The subject is a female in their mid- to late 80s or older, this is a dermoscopic photograph of a skin lesion:
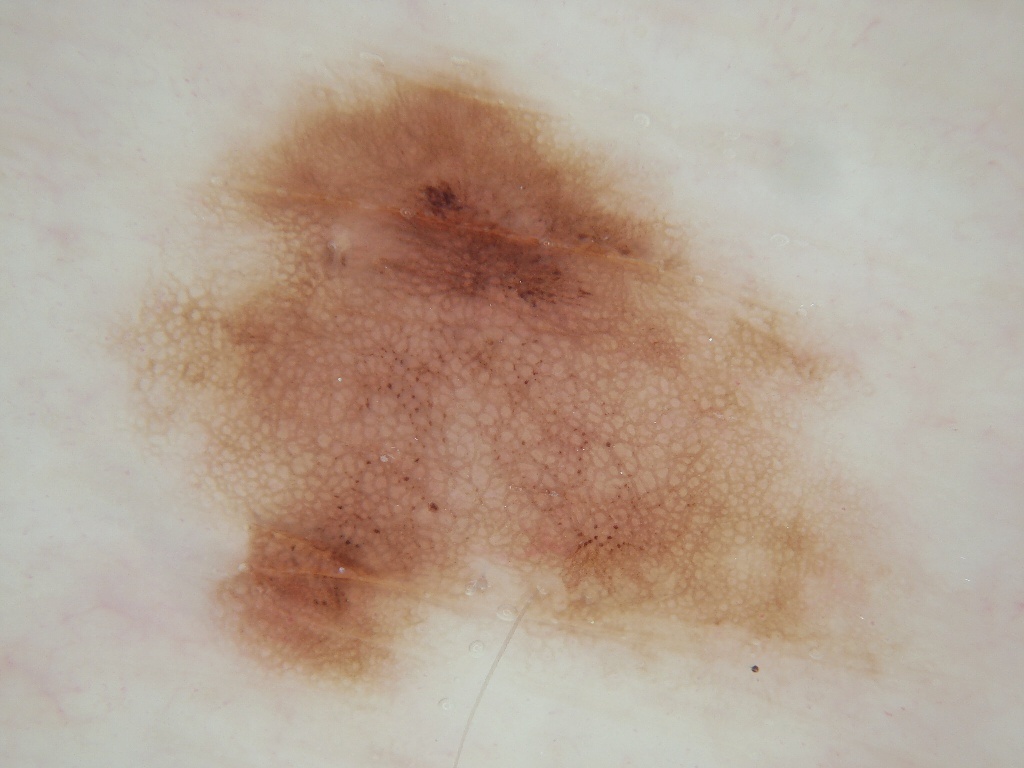Dermoscopic examination shows pigment network, with no negative network, globules, milia-like cysts, or streaks.
The visible lesion spans x1=109, y1=59, x2=911, y2=691.
The lesion takes up a large portion of the image.
Diagnosed as a melanocytic nevus, a benign skin lesion.